A female subject 72 years of age · a dermatoscopic image of a skin lesion · imaged for a research study, with no referral diagnosis recorded: 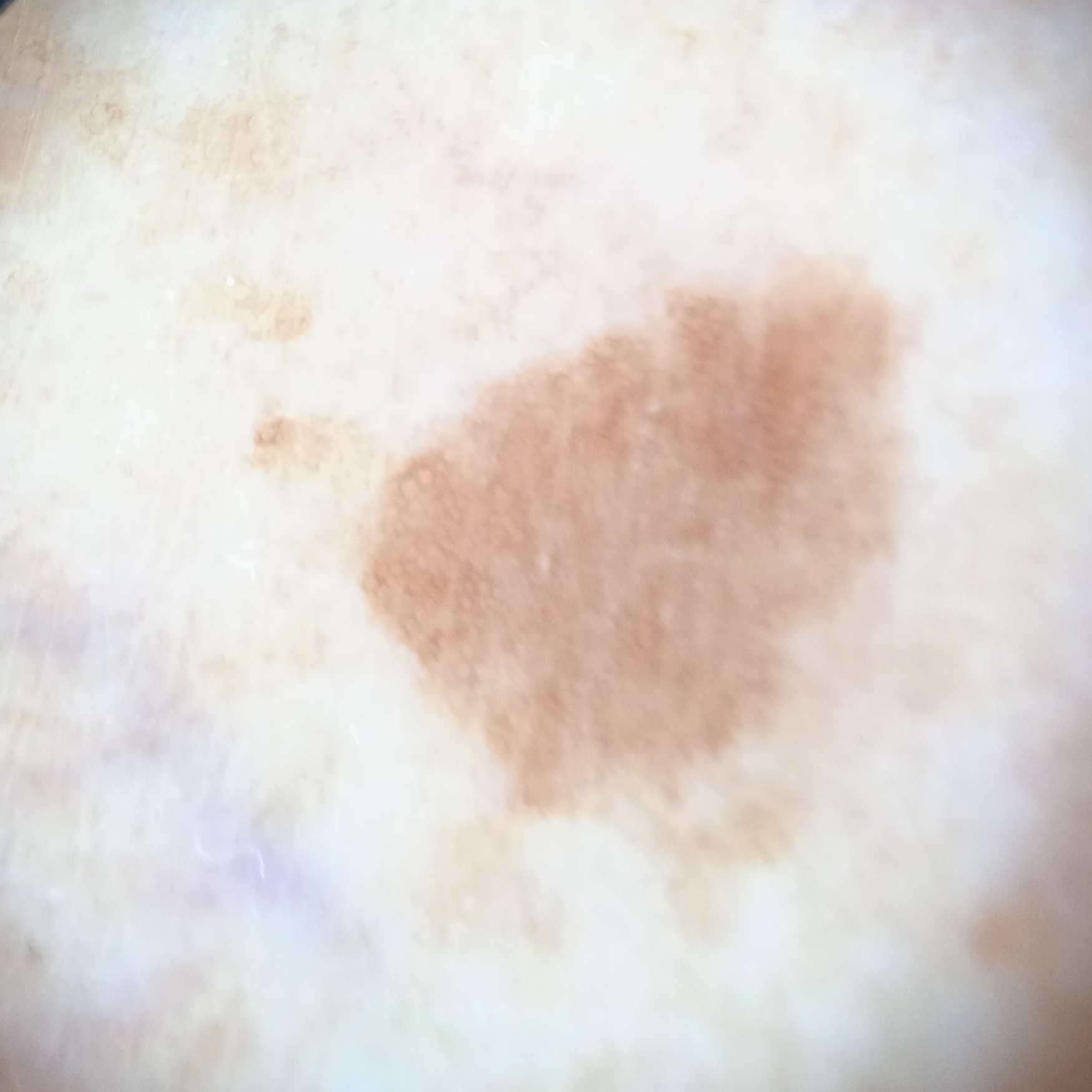Findings:
– body site: a leg
– size: 6.6 mm
– diagnosis: melanocytic nevus (dermatologist consensus)